A dermatoscopic image of a skin lesion.
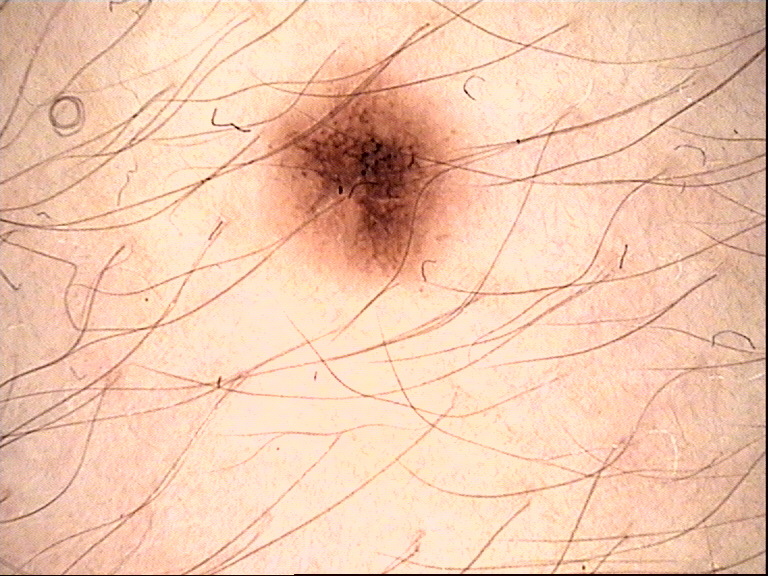Q: What is this lesion?
A: dysplastic junctional nevus (expert consensus)